An image taken at an angle · located on the leg: 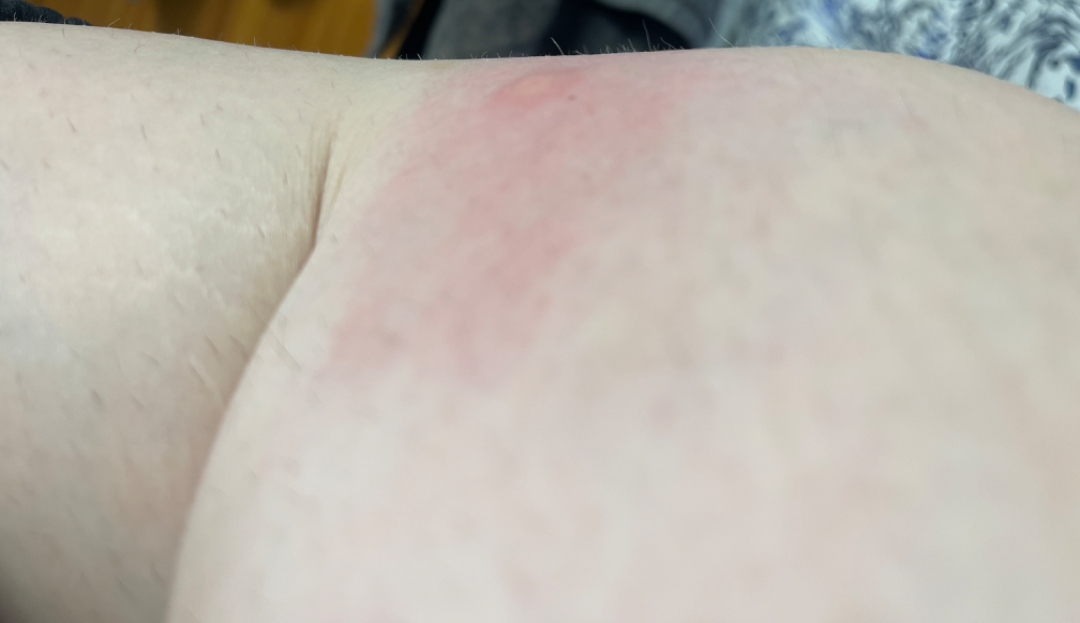The reviewing dermatologist was unable to assign a differential diagnosis from the image. The patient described the issue as a rash. Symptoms reported: itching and enlargement. The patient reports the lesion is raised or bumpy. The patient reports the condition has been present for about one day. No constitutional symptoms were reported.